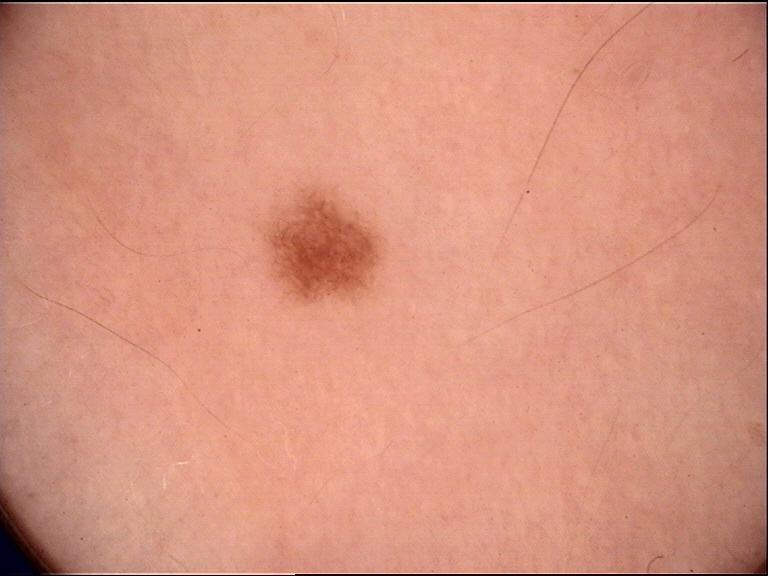Classified as a dysplastic junctional nevus.